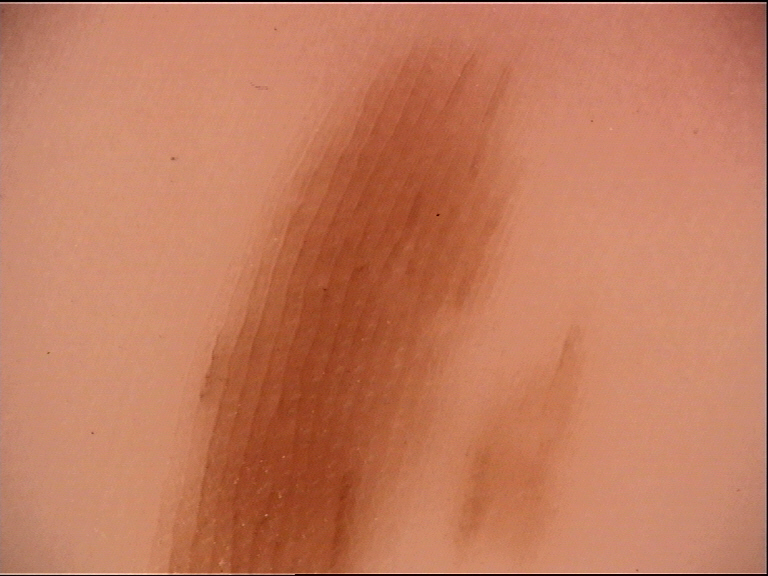Impression:
Consistent with a banal lesion — an acral junctional nevus.